Texture is reported as raised or bumpy, skin tone: FST III; human graders estimated Monk skin tone scale 3 (US pool) or 2 (India pool), a close-up photograph, the subject is a female aged 40–49, self-categorized by the patient as a rash, the lesion is associated with itching, reported duration is one to four weeks, located on the palm: 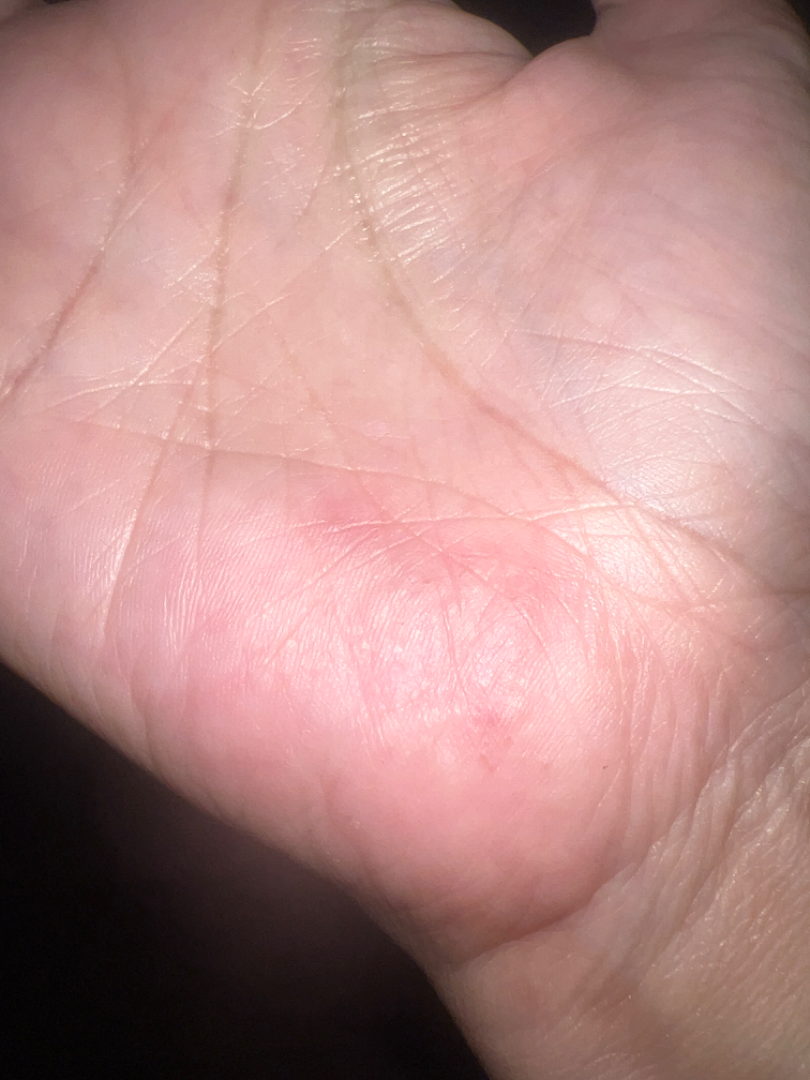differential diagnosis: favoring Eczema.